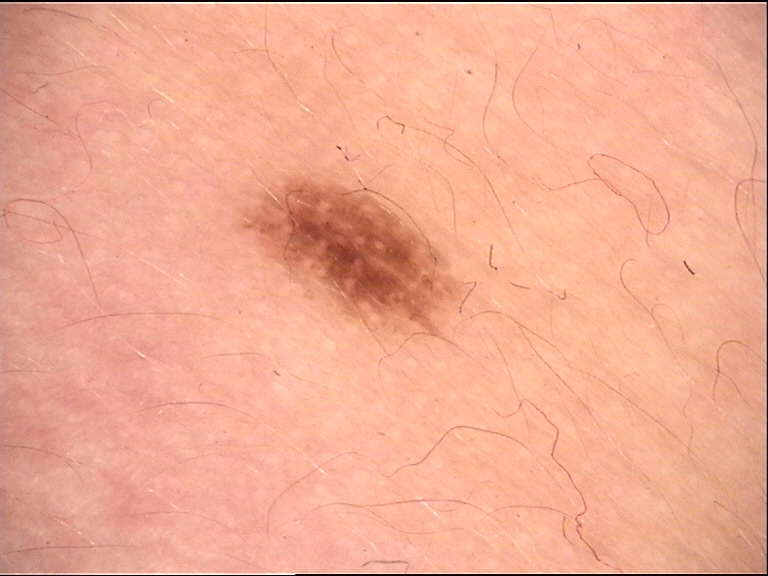A dermatoscopic image of a skin lesion. The architecture is that of a banal lesion. Diagnosed as a junctional nevus.